Female contributor, age 40–49. The patient also reports shortness of breath and fatigue. The lesion is described as raised or bumpy. FST III. A close-up photograph. The head or neck and arm are involved. Reported lesion symptoms include itching and bothersome appearance — 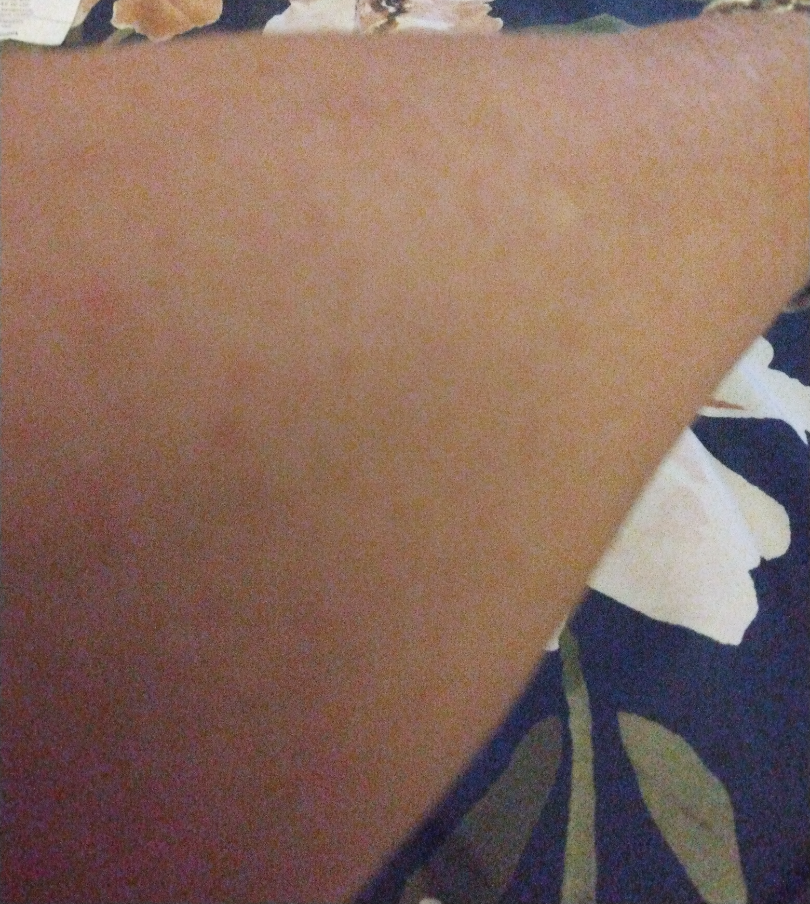Q: Could the case be diagnosed?
A: indeterminate